A male subject approximately 75 years of age; a clinical photograph showing a skin lesion in context; the patient is Fitzpatrick skin type II: 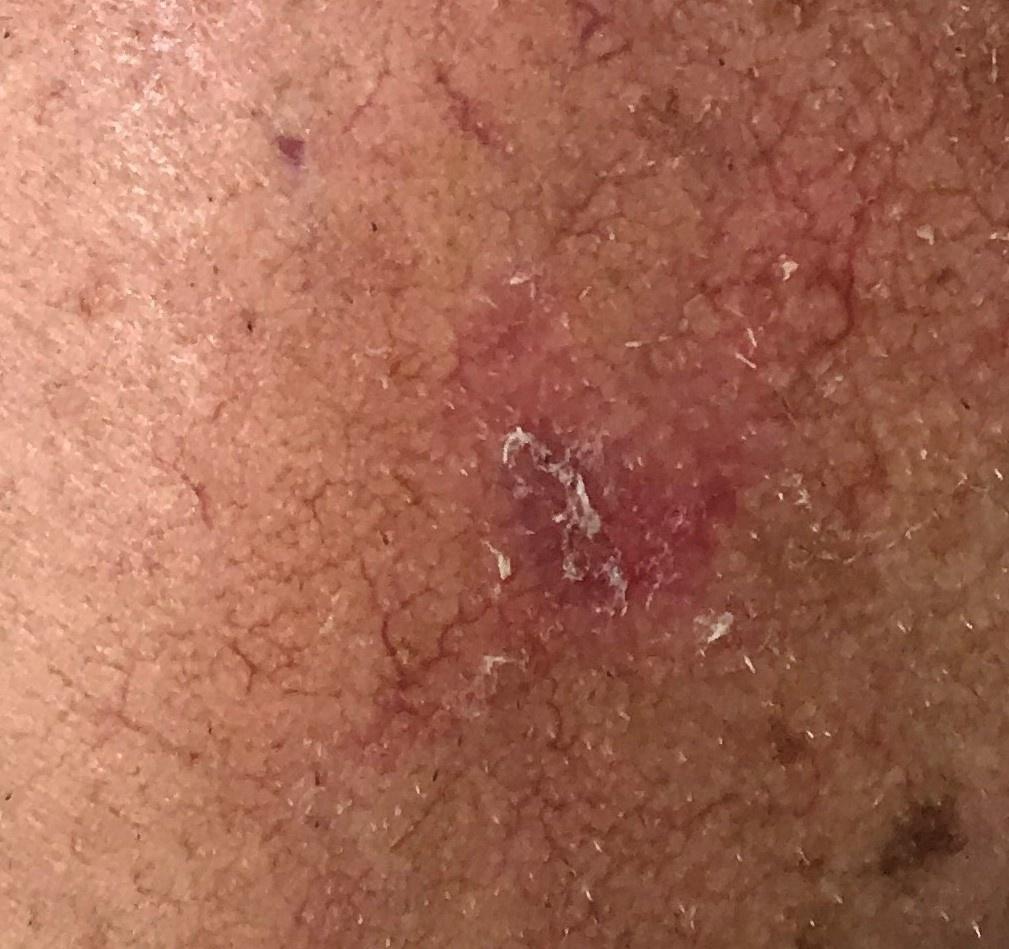The lesion was found on the head or neck. Histopathology confirmed a tumor of follicular differentiation — a basal cell carcinoma.